A dermatoscopic image of a skin lesion: 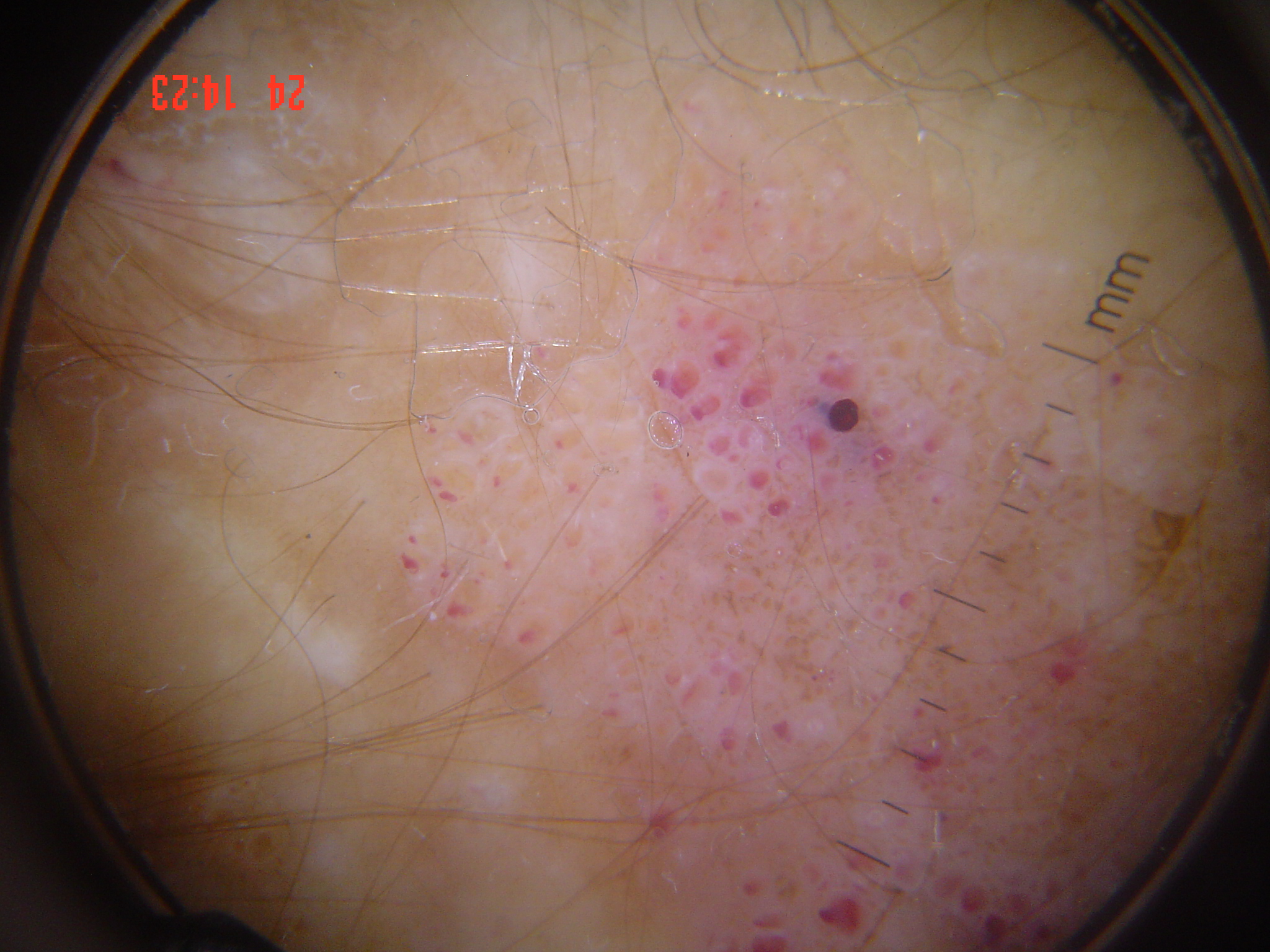This is a vascular lesion. Labeled as a lymphangioma.